Symptoms reported: enlargement and itching · close-up view · the patient notes the condition has been present for less than one week · the lesion is described as raised or bumpy — 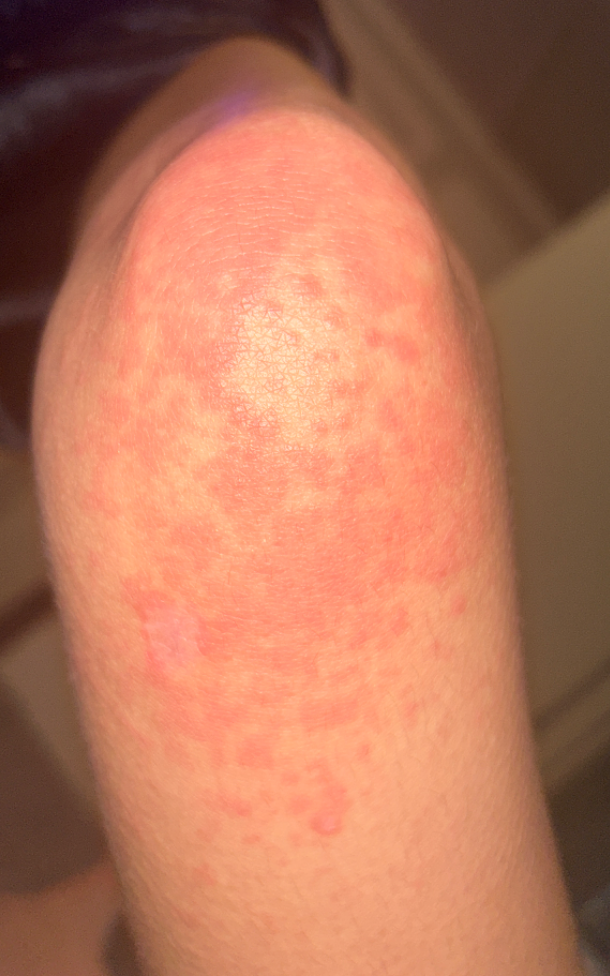Notes:
- dermatologist impression — Urticaria (41%); Eczema (41%); Pityriasis rubra pilaris (18%)